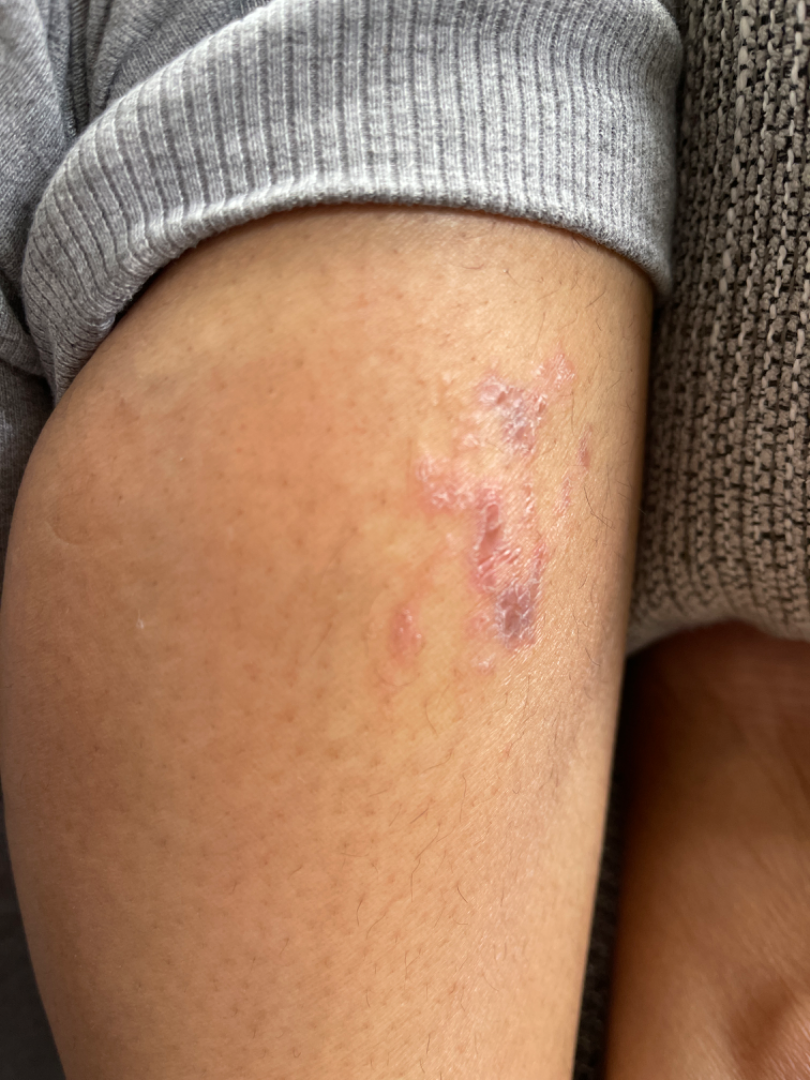{
  "body_site": "leg",
  "patient": "female, age 30–39",
  "shot_type": "at an angle",
  "differential": {
    "leading": [
      "Eczema"
    ],
    "unlikely": [
      "Tinea",
      "Cutaneous larva migrans",
      "Lichen planus/lichenoid eruption",
      "Allergic Contact Dermatitis"
    ]
  }
}